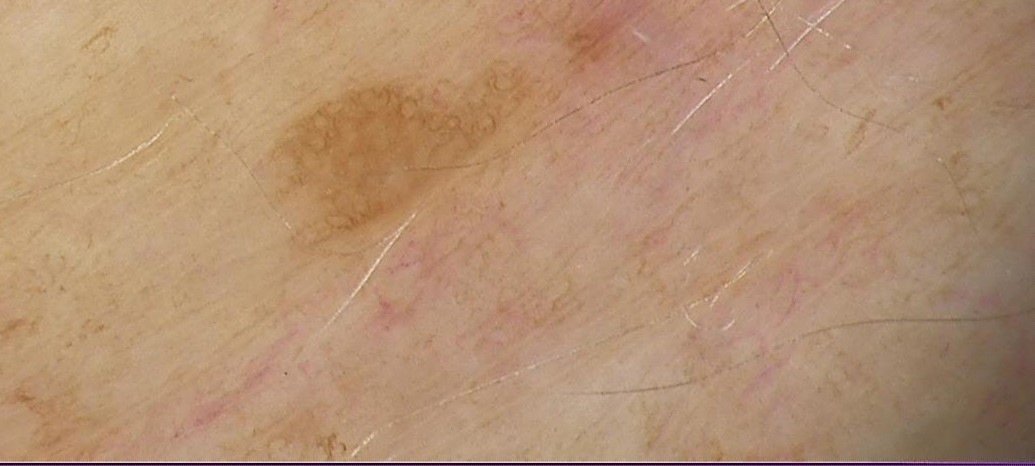* modality · dermatoscopy
* category · keratinocytic
* class · seborrheic keratosis (expert consensus)